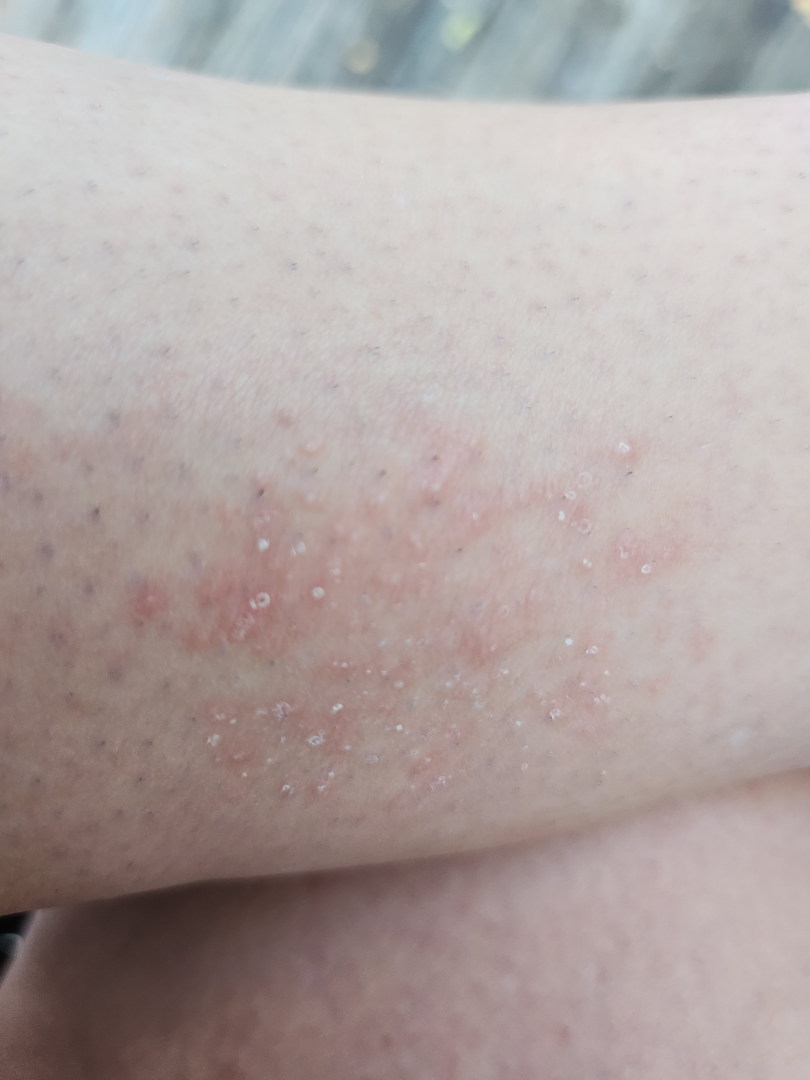Patient information:
Female contributor, age 30–39. Located on the leg. This image was taken at an angle. The lesion is described as raised or bumpy. The lesion is associated with itching. Self-categorized by the patient as a rash.
Review:
A single dermatologist reviewed the case: Keratosis pilaris and Lichen spinulosus were considered with similar weight; a remote consideration is Folliculitis.